This is a close-up image.
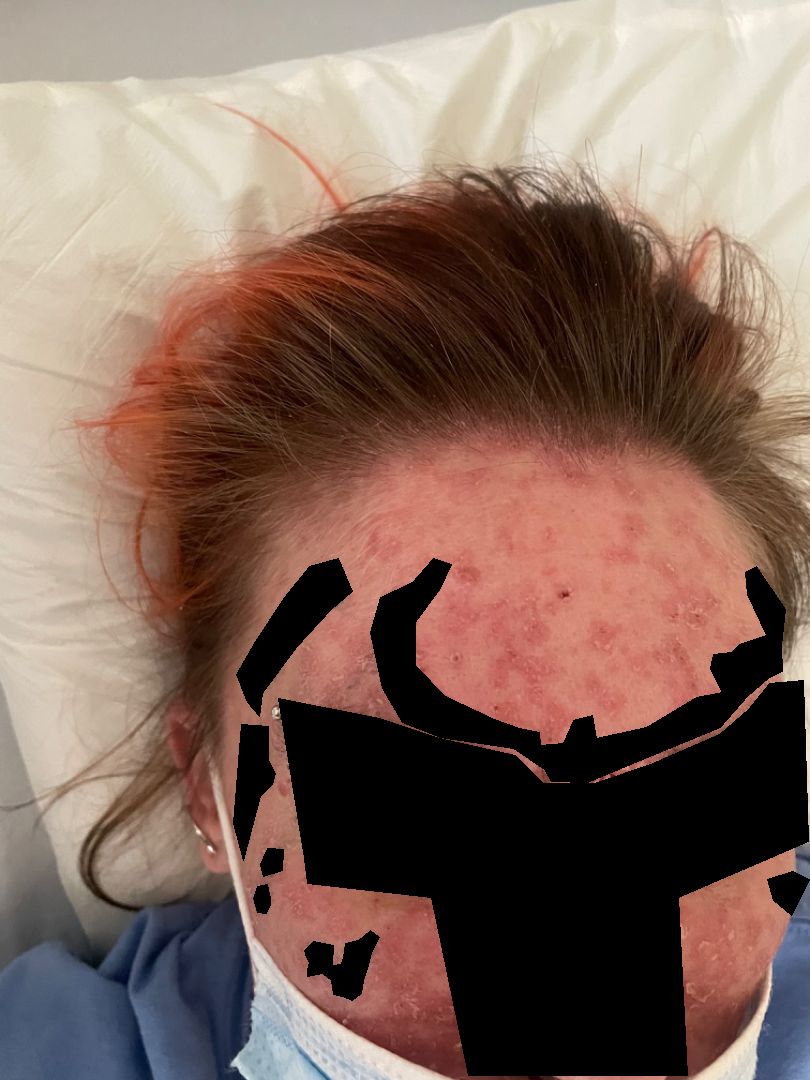Diagnostic features were not clearly distinguishable in this photograph.